The photo was captured at a distance; the affected area is the arm and front of the torso; the contributor is 50–59, male:
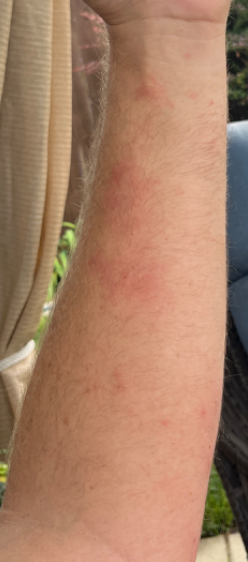Q: What was the assessment?
A: unable to determine